The contributor is a female aged 18–29 · the contributor notes itching · the lesion is described as raised or bumpy · present for less than one week · this is a close-up image · the patient described the issue as a rash: 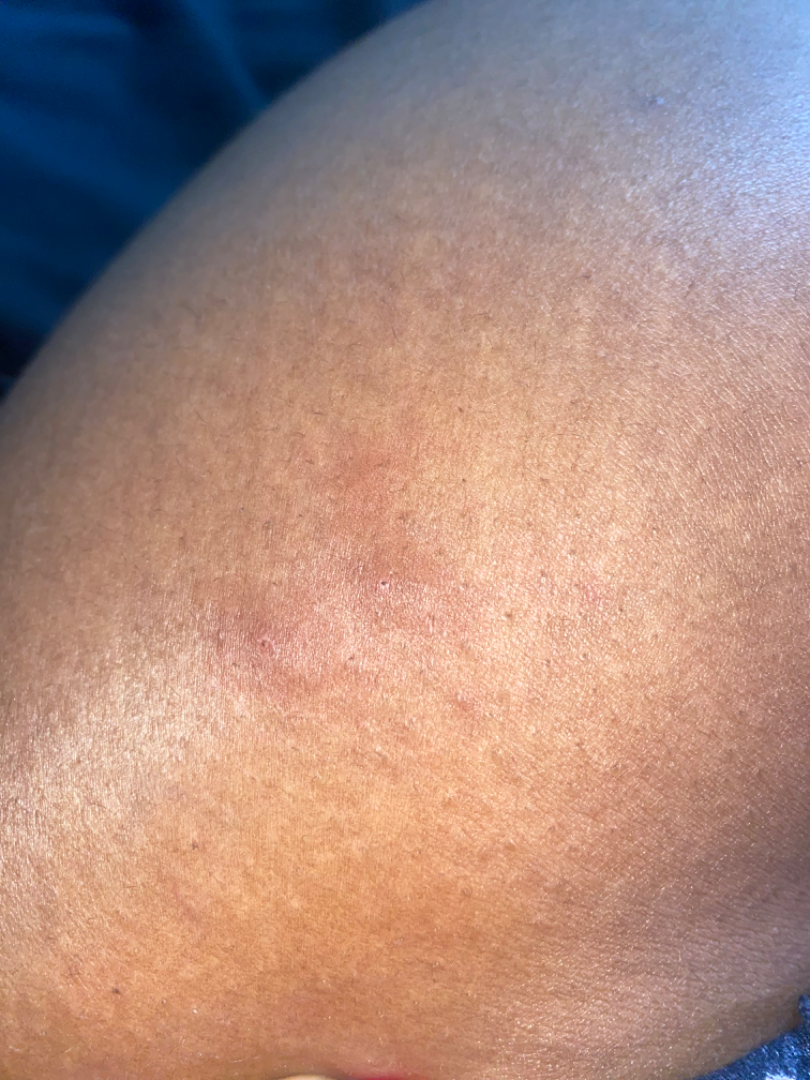Q: What is the differential diagnosis?
A: Insect Bite and Cyst were each considered, in no particular order; less probable is Adnexal neoplasm; less likely is Urticaria; a more distant consideration is Eczema